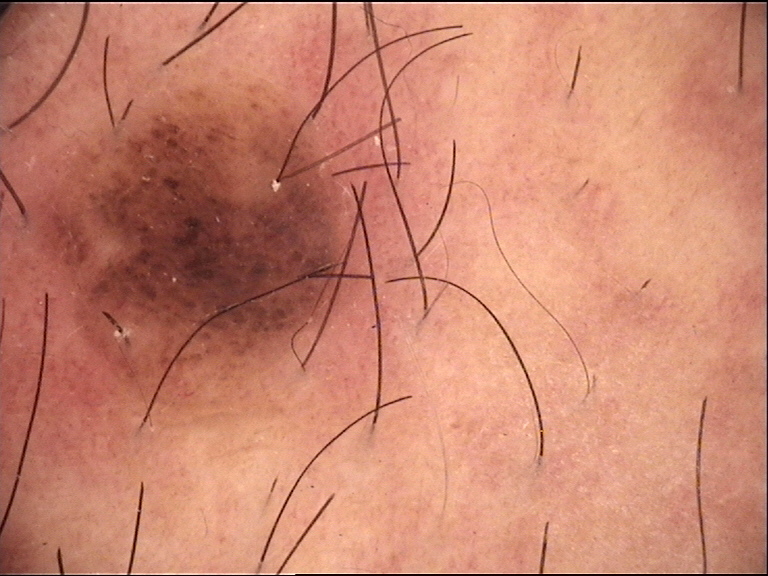• assessment — dysplastic compound nevus (expert consensus)